Recorded as Fitzpatrick skin type III; a female subject roughly 50 years of age; contact-polarized dermoscopy of a skin lesion.
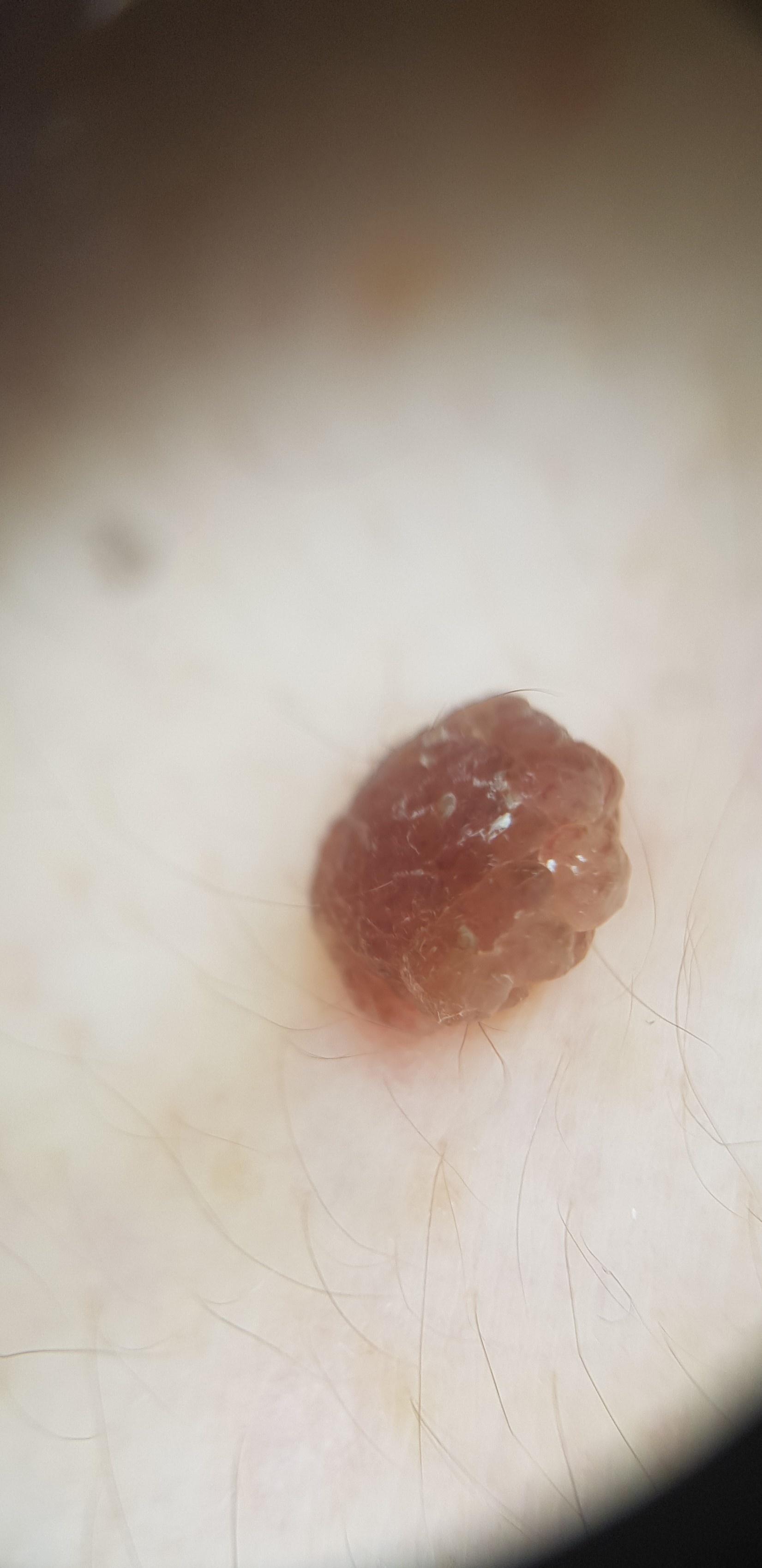Q: What did the workup show?
A: Nevus (biopsy-proven)